The patient is a female aged 18–29; this image was taken at an angle — 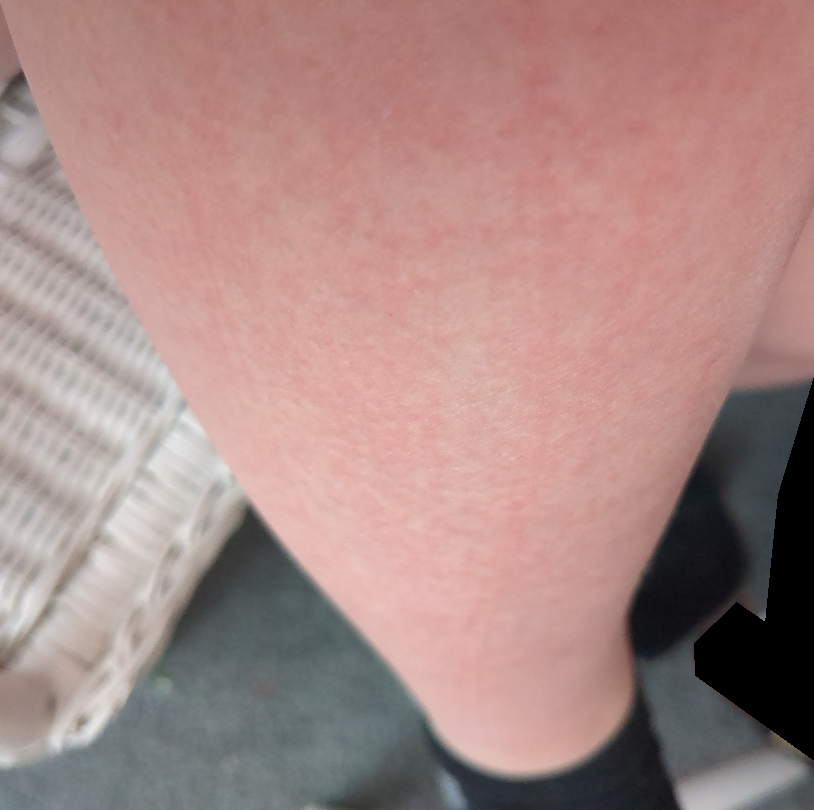assessment: ungradable on photographic review
associated systemic symptoms: none reported
lesion symptoms: burning and bothersome appearance